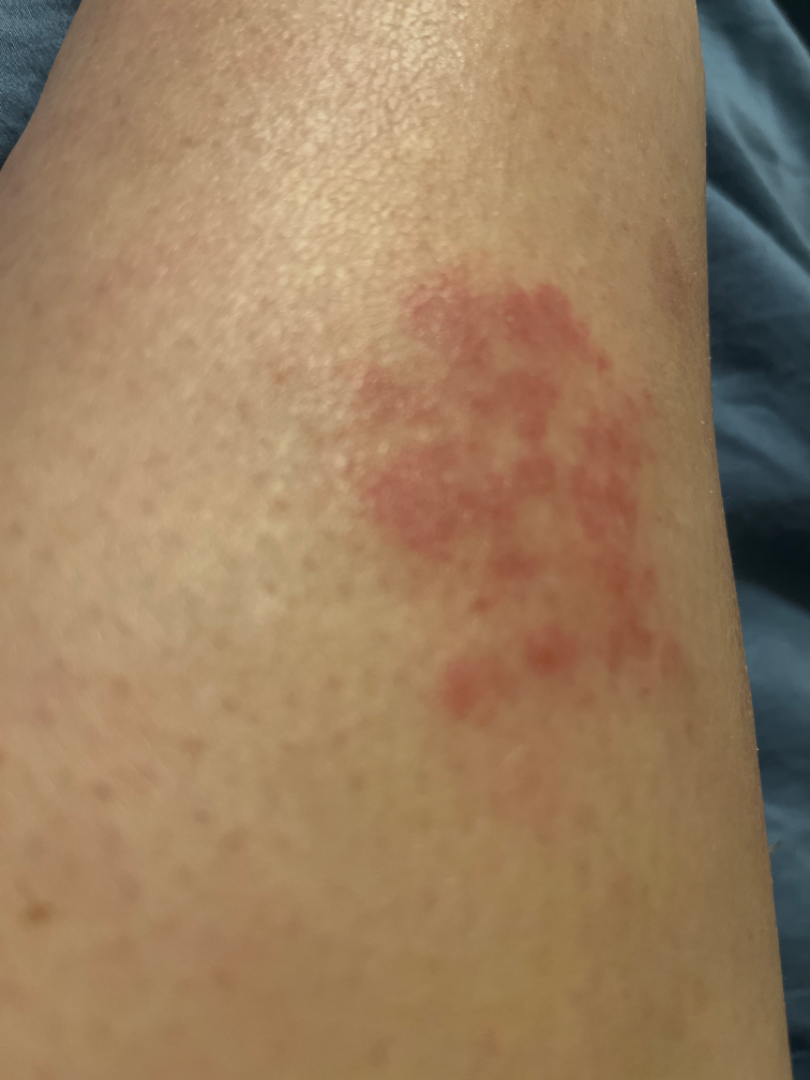Assessment: The dermatologist could not determine a likely condition from the photograph alone. Clinical context: Present for about one day. Located on the leg. The lesion is described as flat. The patient described the issue as a rash. The photo was captured at an angle.